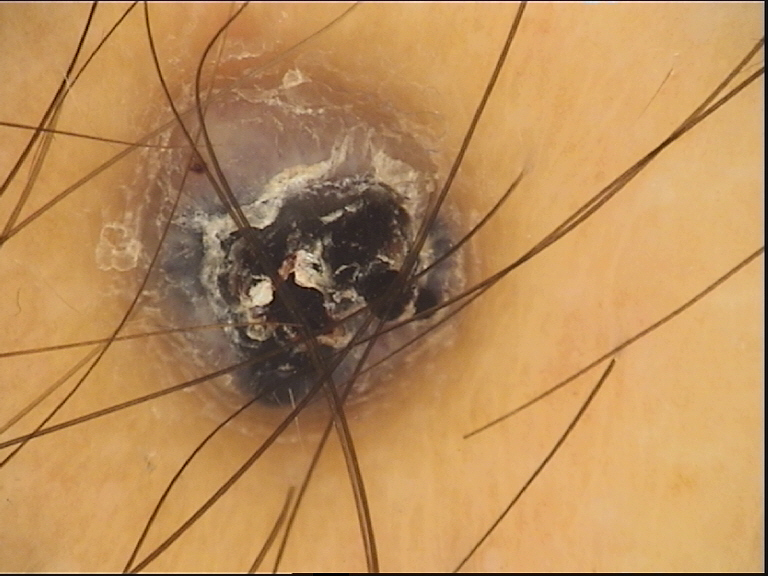Confirmed on histopathology as a melanoma.